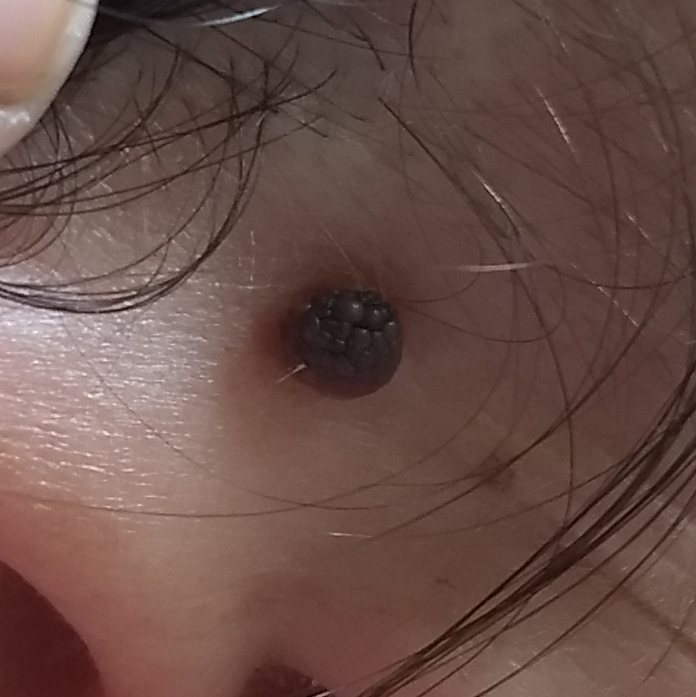The clinical impression was a nevus.